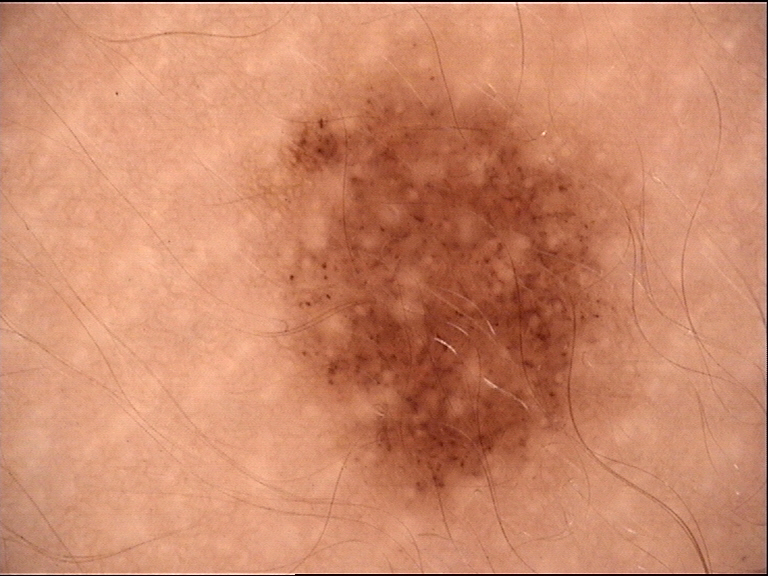The diagnosis was a congenital junctional nevus.